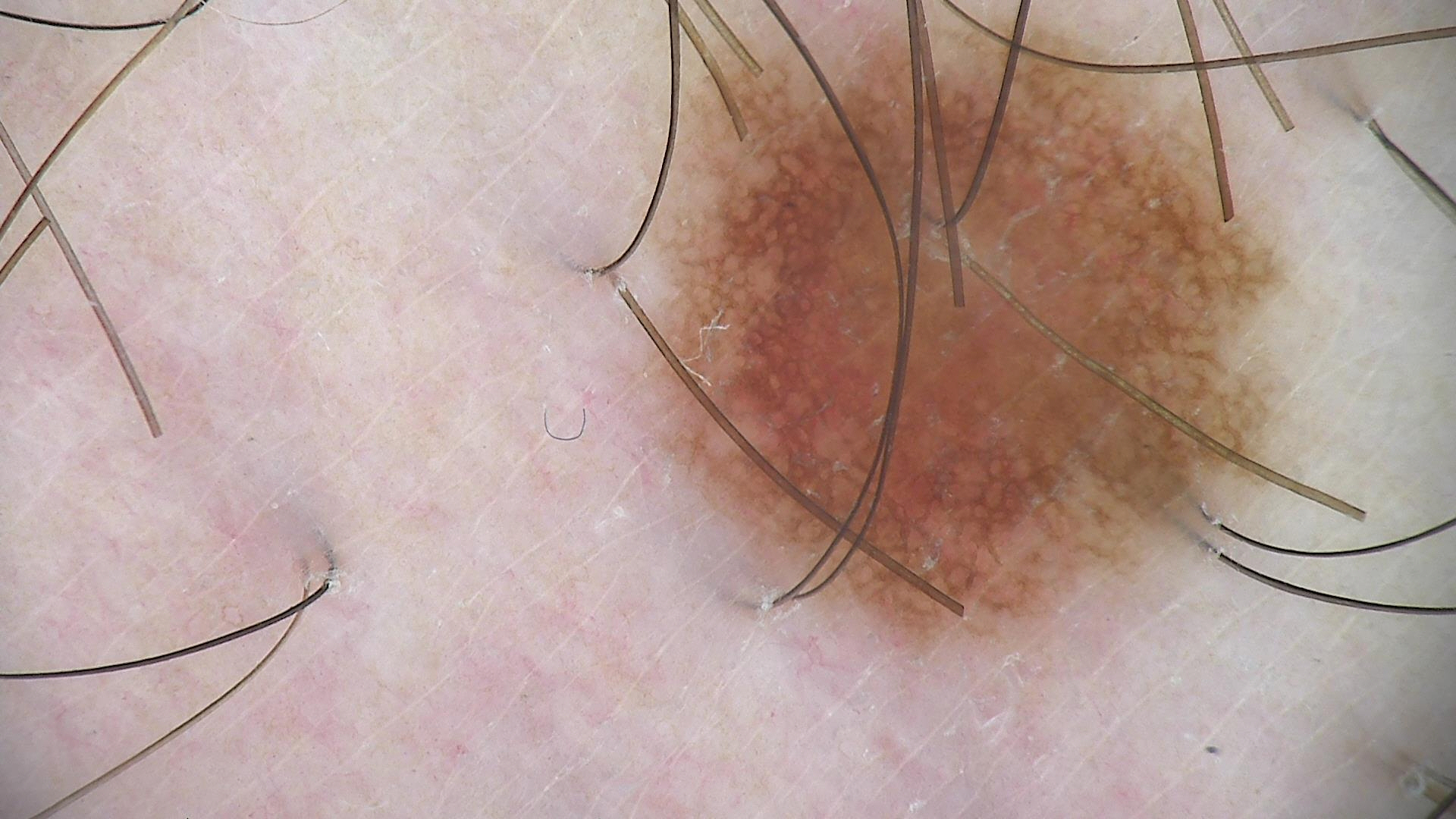class: dysplastic junctional nevus (expert consensus).